A dermoscopic photograph of a skin lesion:
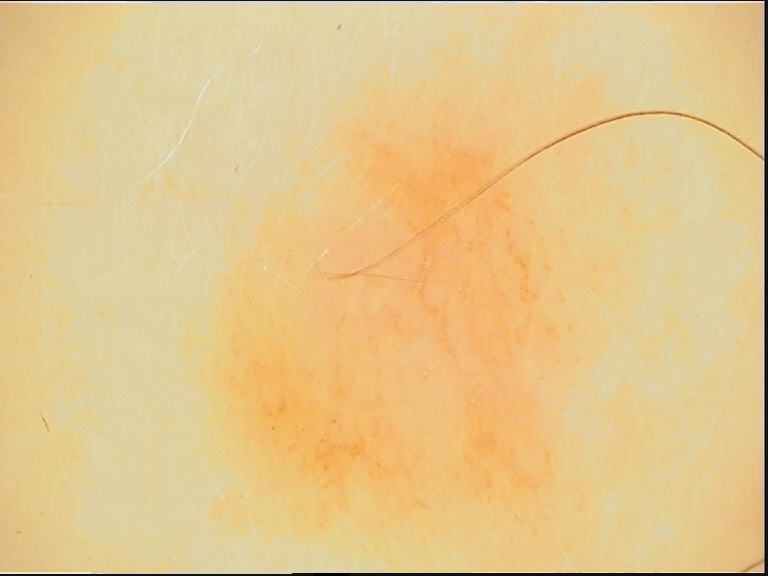Conclusion: Classified as a banal lesion — a junctional nevus.